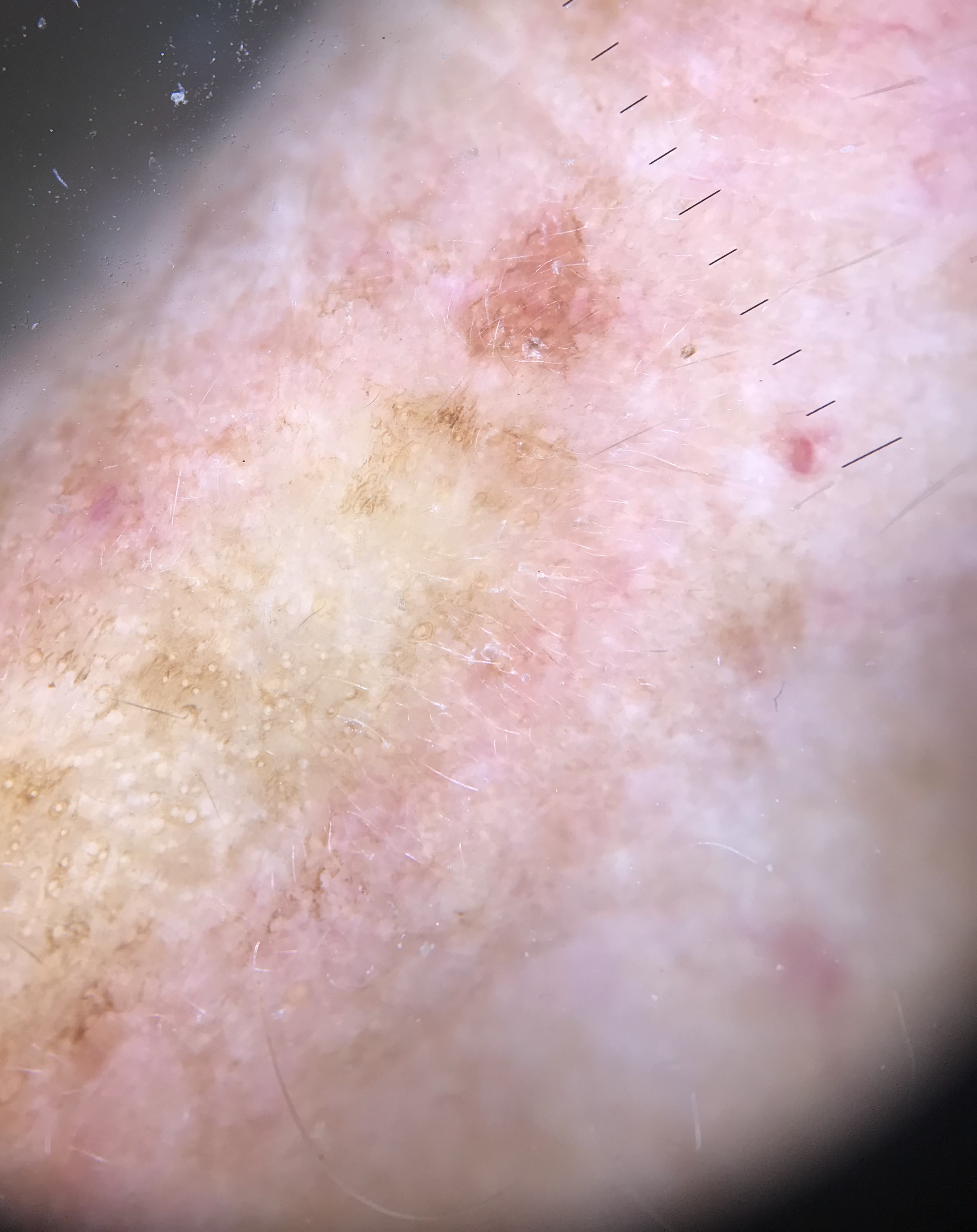A skin lesion imaged with a dermatoscope. The architecture is that of a keratinocytic lesion. Classified as an actinic keratosis.